A dermoscopic image of a skin lesion.
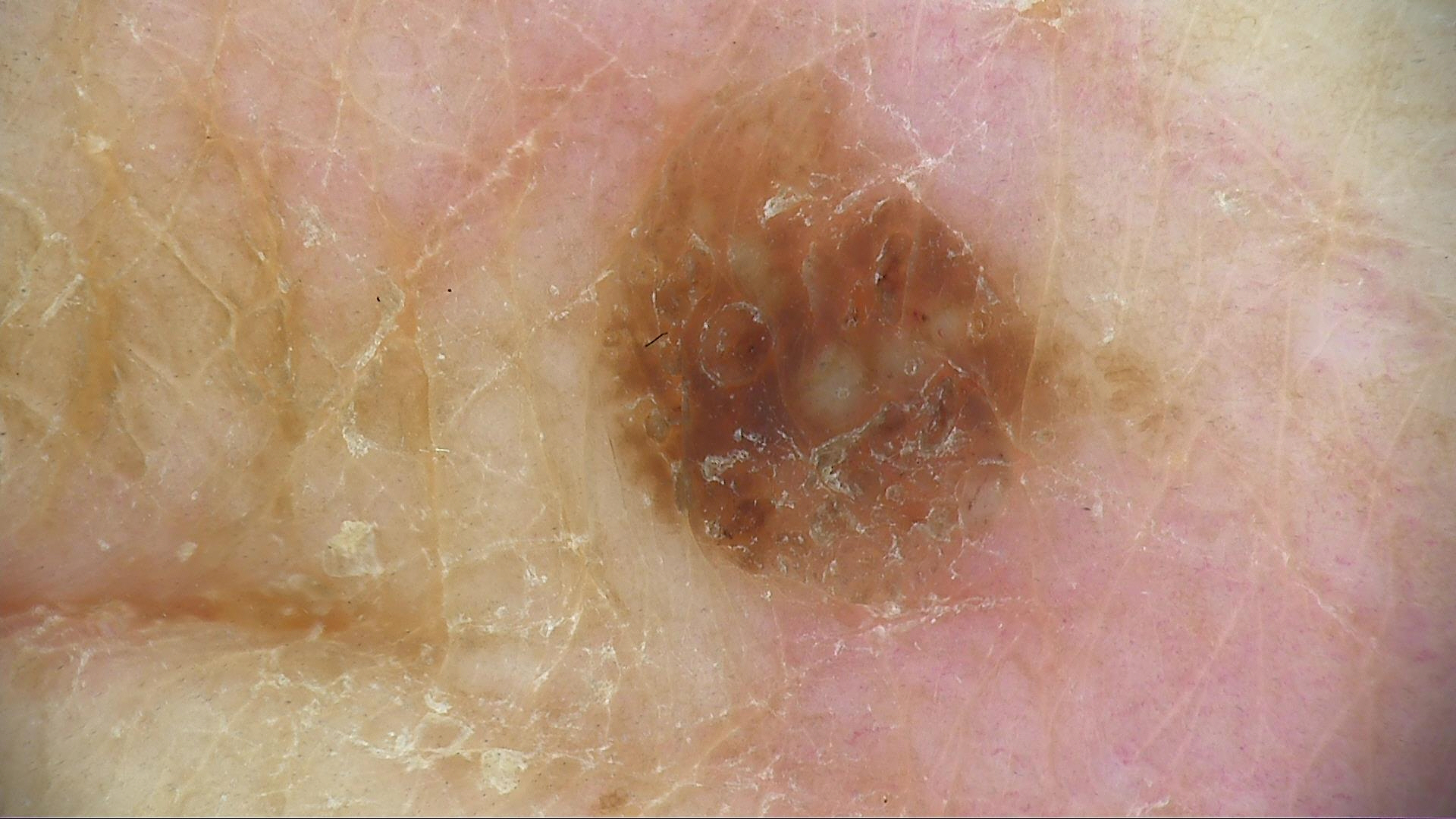Labeled as a keratinocytic lesion — a seborrheic keratosis.